The arm is involved. The contributor is 30–39, female. The photo was captured at a distance.
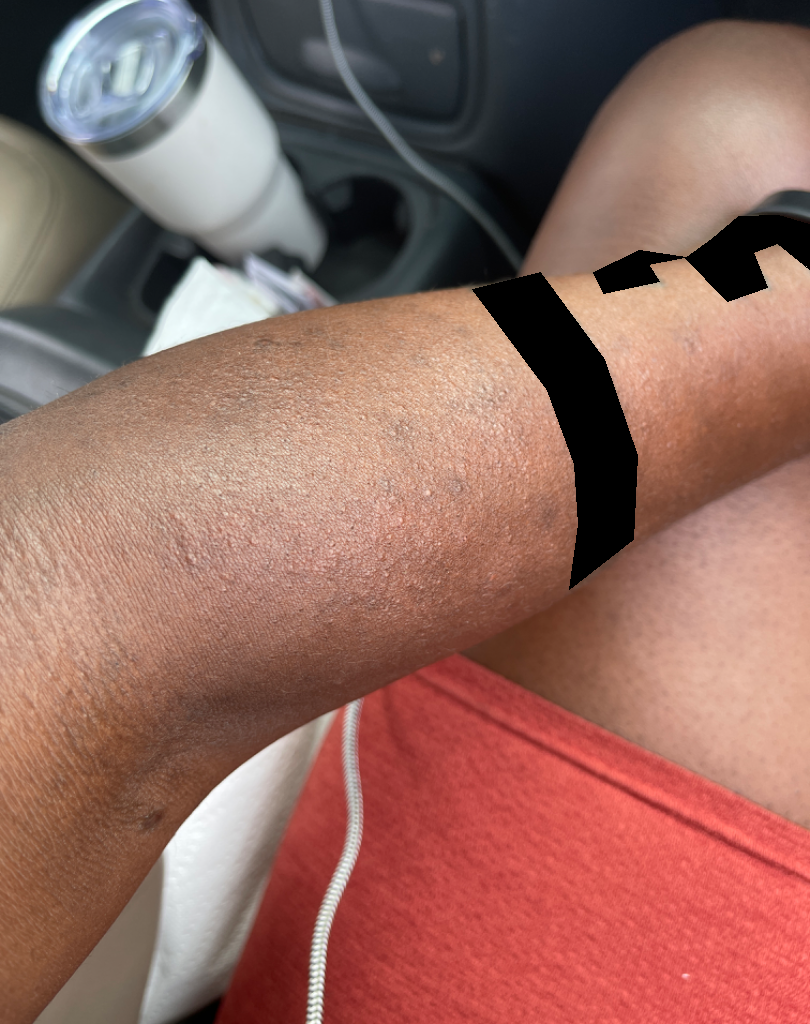Clinical context: The contributor notes the condition has been present for one to four weeks. The contributor notes the lesion is raised or bumpy and rough or flaky. Reported lesion symptoms include bothersome appearance and itching. Assessment: The reviewing panel's impression was: Eczema (possible); Allergic Contact Dermatitis (possible); Photodermatitis (remote).